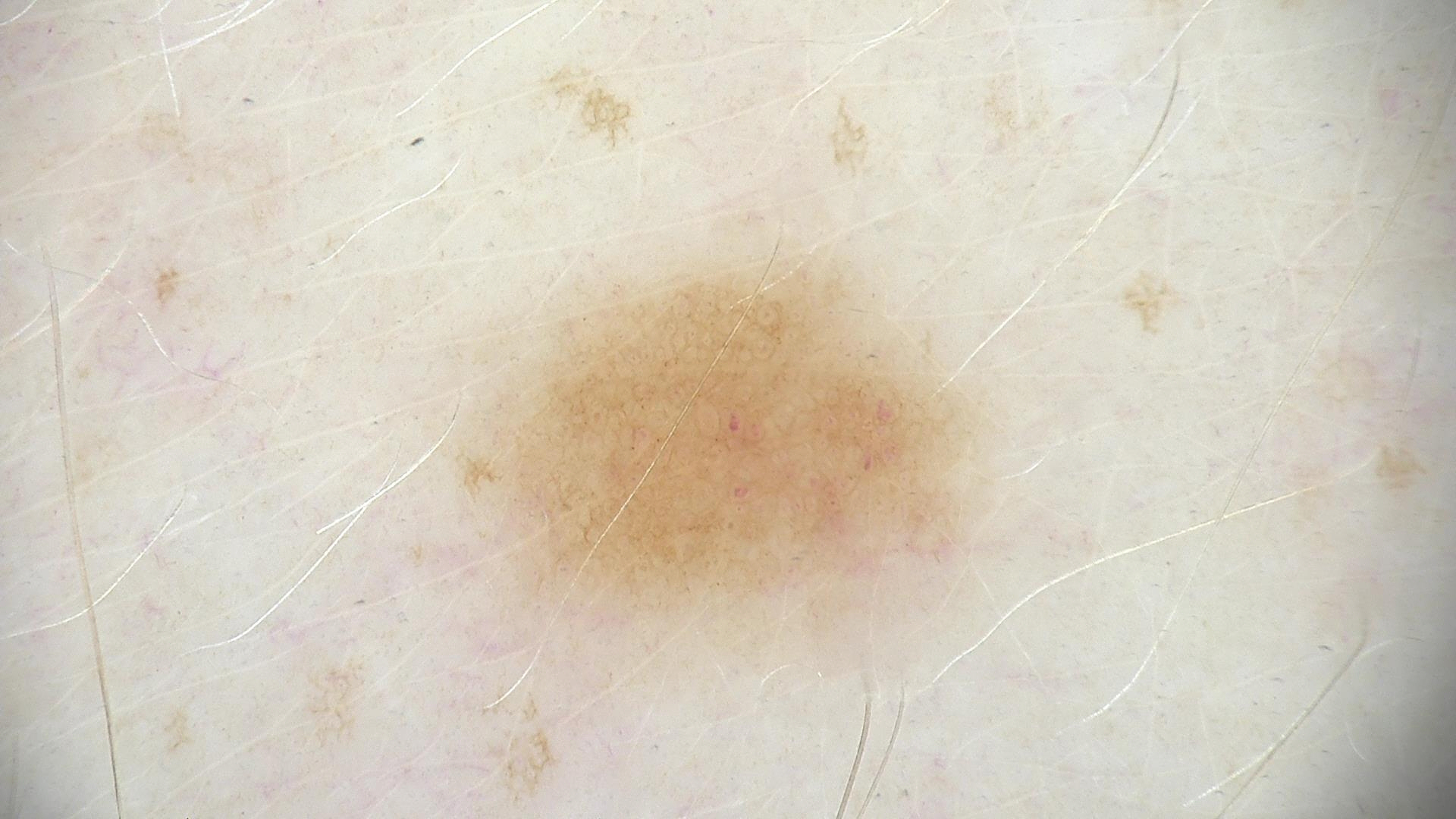Conclusion:
Consistent with a benign lesion — a dysplastic junctional nevus.